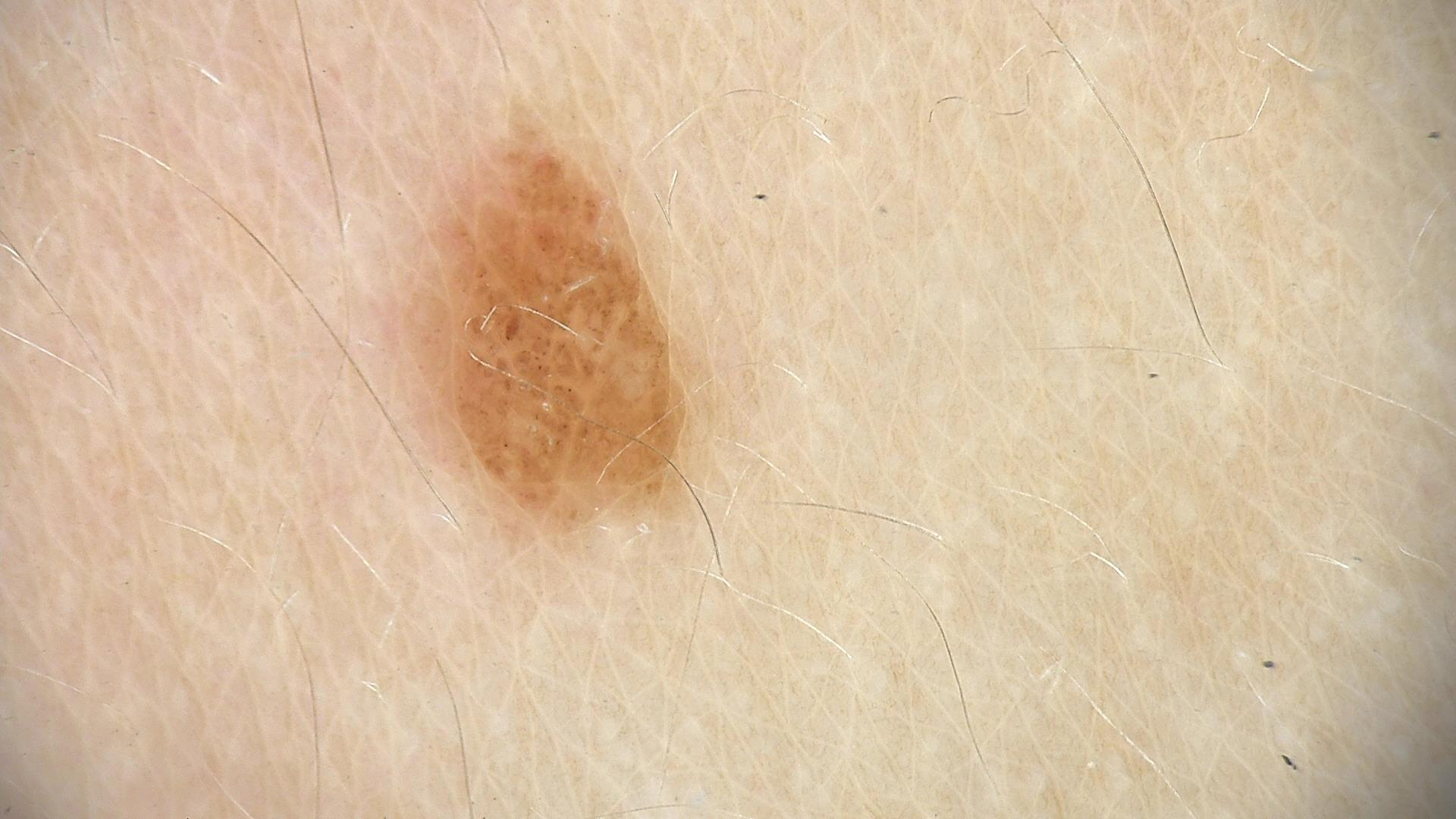Diagnosed as a compound nevus.